By history, alcohol use, pesticide exposure, and no prior skin cancer (patient or family); a male patient in their early 60s: 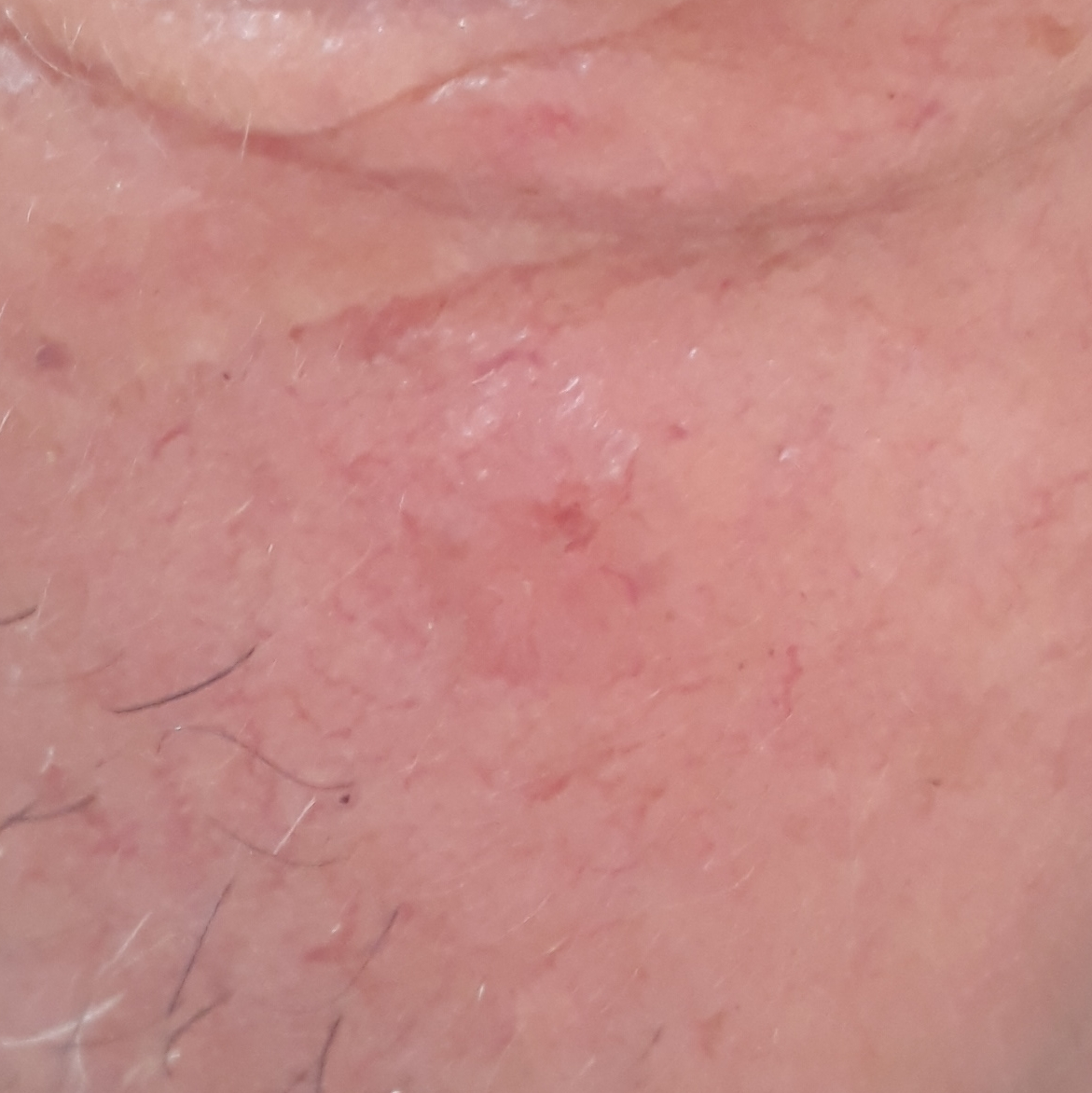<lesion>
  <lesion_location>the face</lesion_location>
  <lesion_size>
    <diameter_1_mm>12.0</diameter_1_mm>
    <diameter_2_mm>10.0</diameter_2_mm>
  </lesion_size>
  <diagnosis>
    <name>basal cell carcinoma</name>
    <code>BCC</code>
    <malignancy>malignant</malignancy>
    <confirmation>histopathology</confirmation>
  </diagnosis>
</lesion>